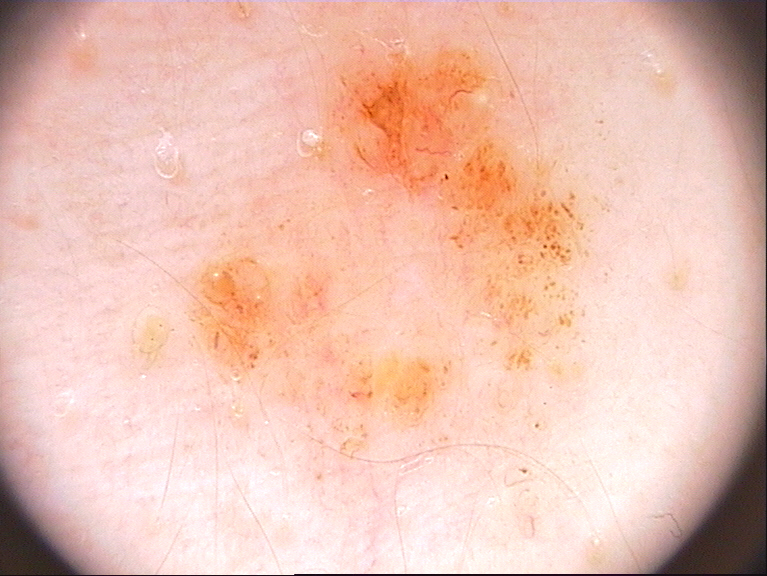{"image": {"modality": "dermoscopy"}, "dermoscopic_features": {"present": ["globules"], "absent": ["streaks", "milia-like cysts", "pigment network", "negative network"]}, "lesion_location": {"bbox_xyxy": [123, 16, 638, 523]}, "diagnosis": {"name": "melanocytic nevus", "malignancy": "benign", "lineage": "melanocytic", "provenance": "clinical"}}